The photo was captured at a distance; the patient is 30–39, female; the lesion involves the top or side of the foot: 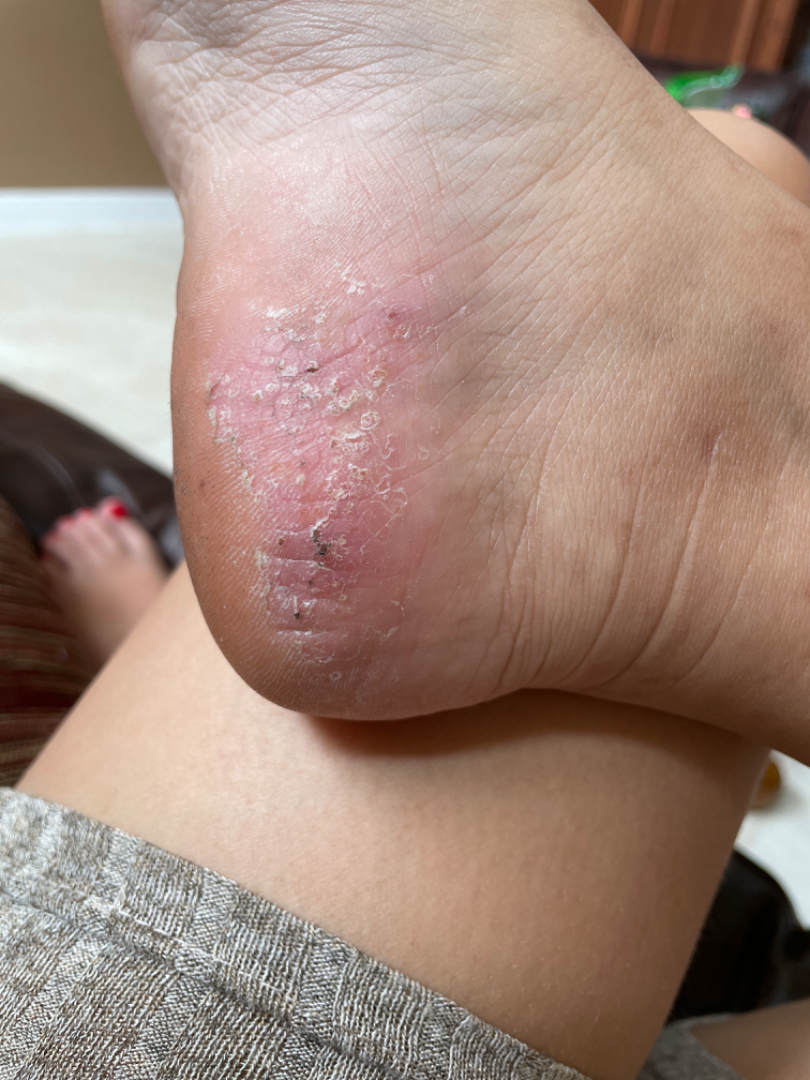Texture is reported as rough or flaky, fluid-filled and raised or bumpy. Present for more than one year. Reported lesion symptoms include itching. On photographic review, the leading impression is Tinea; possibly Eczema.